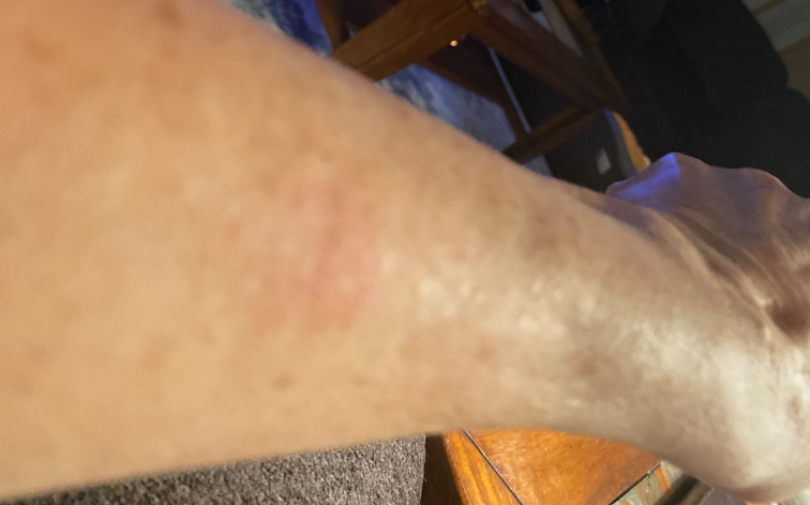| key | value |
|---|---|
| assessment | could not be assessed |
| body site | arm |
| view | at an angle |